A dermoscopy image of a single skin lesion.
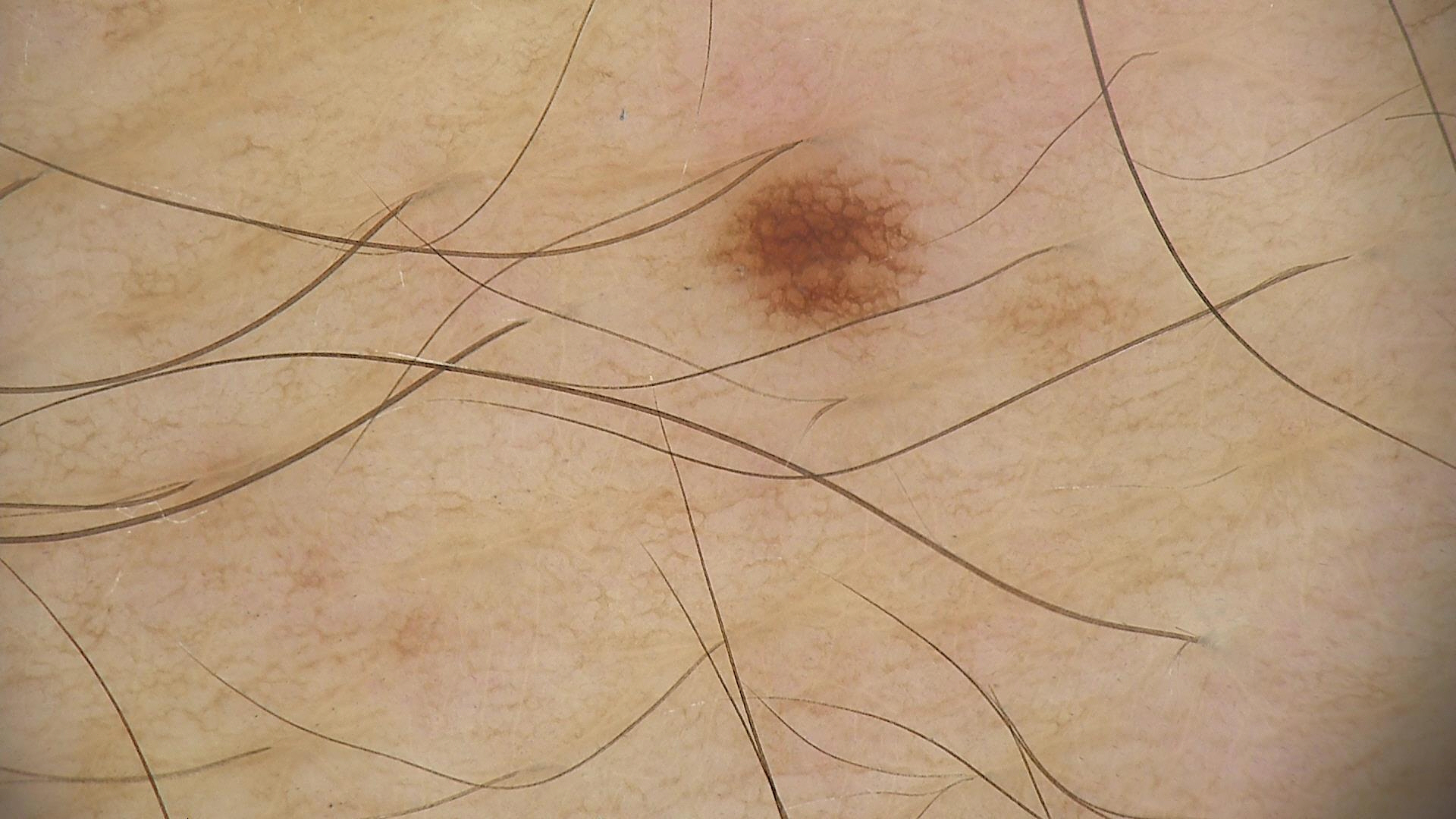diagnostic label=dysplastic junctional nevus (expert consensus).